A dermatoscopic image of a skin lesion. A female subject, aged around 40 — 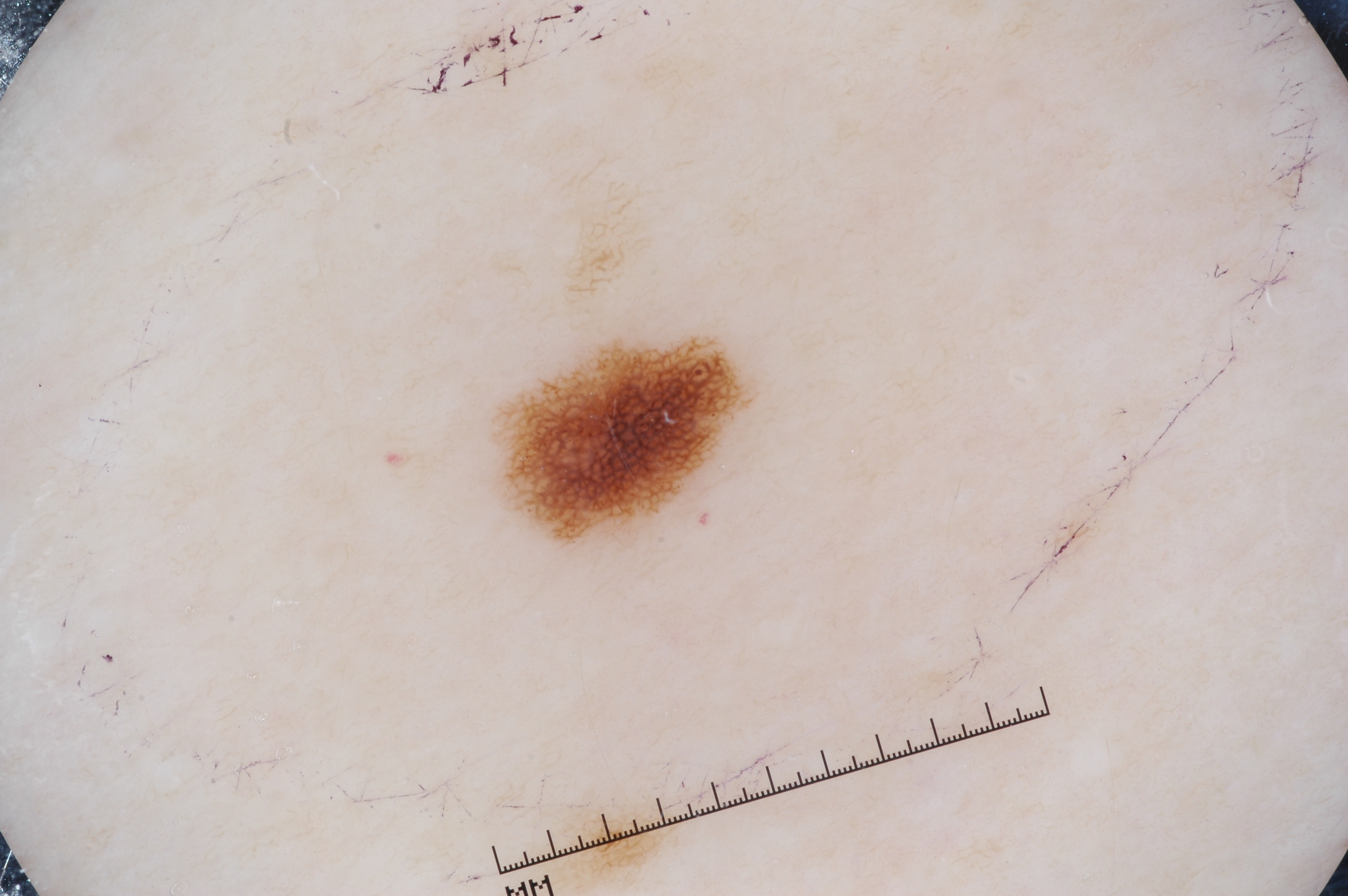A small lesion within a wider field of skin. In (x1, y1, x2, y2) order, the lesion spans <bbox>506, 336, 747, 546</bbox>. Dermoscopically, the lesion shows pigment network, with no milia-like cysts, streaks, or negative network. Consistent with a melanocytic nevus, a benign lesion.